A dermoscopic close-up of a skin lesion:
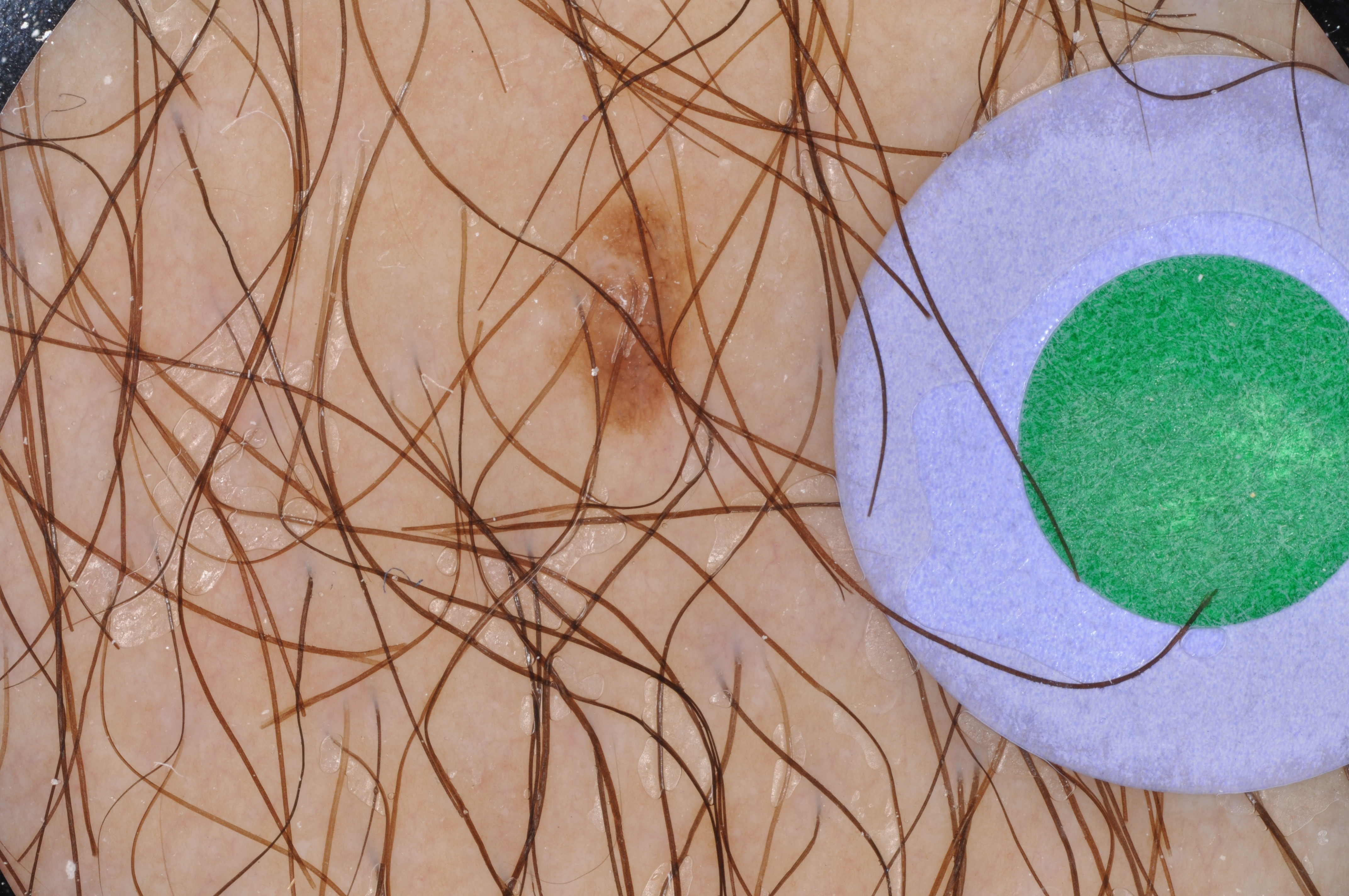Image and clinical context: The lesion's extent is x1=534 y1=166 x2=724 y2=459. Impression: Expert review diagnosed this as a melanocytic nevus.